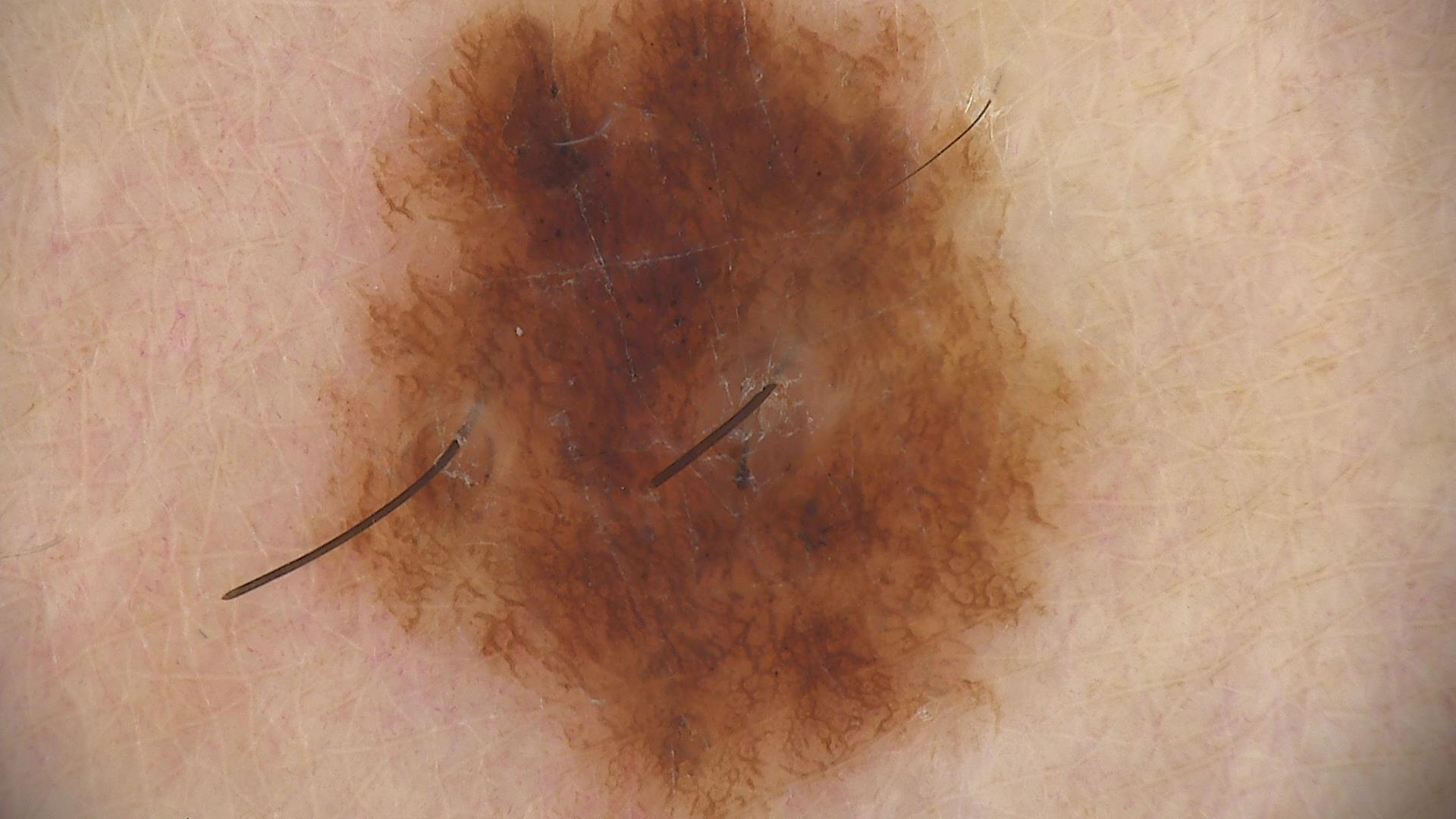<lesion>
  <diagnosis>
    <name>dysplastic compound nevus</name>
    <code>cd</code>
    <malignancy>benign</malignancy>
    <super_class>melanocytic</super_class>
    <confirmation>expert consensus</confirmation>
  </diagnosis>
</lesion>